The subject is a male aged 30–39; the affected area is the arm, back of the hand, leg and top or side of the foot; the photo was captured at a distance:
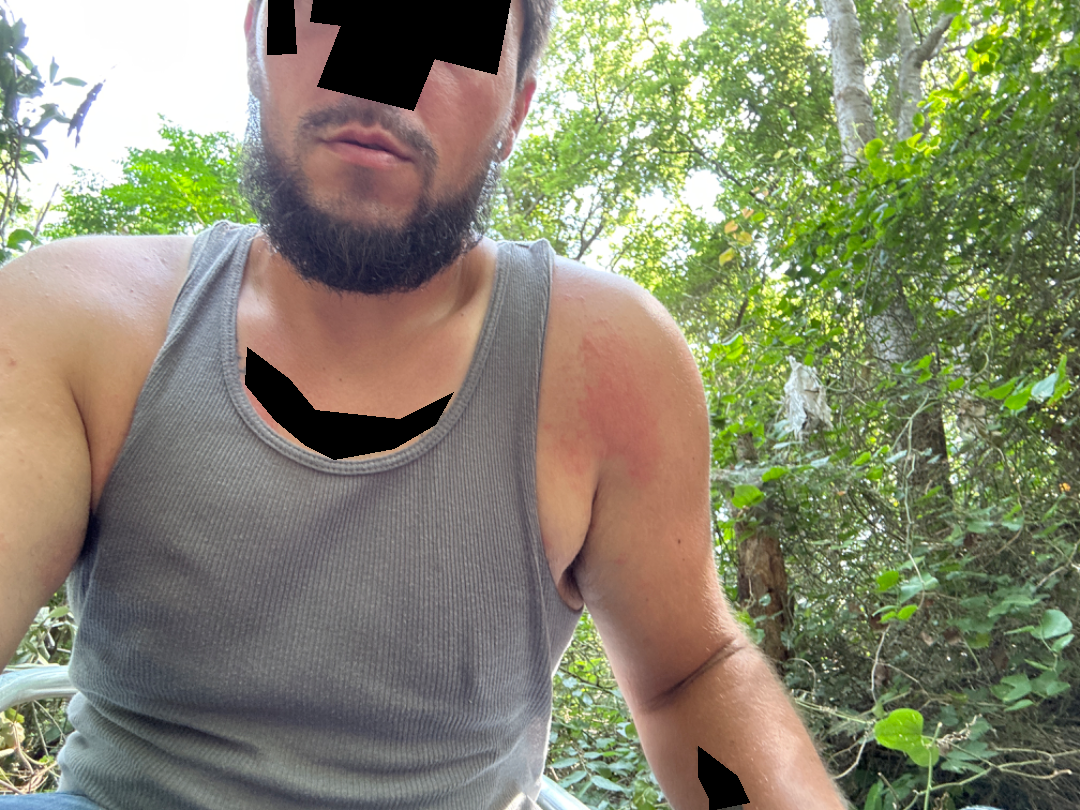On remote dermatologist review: the impression was split between Acute dermatitis, NOS and Allergic Contact Dermatitis.